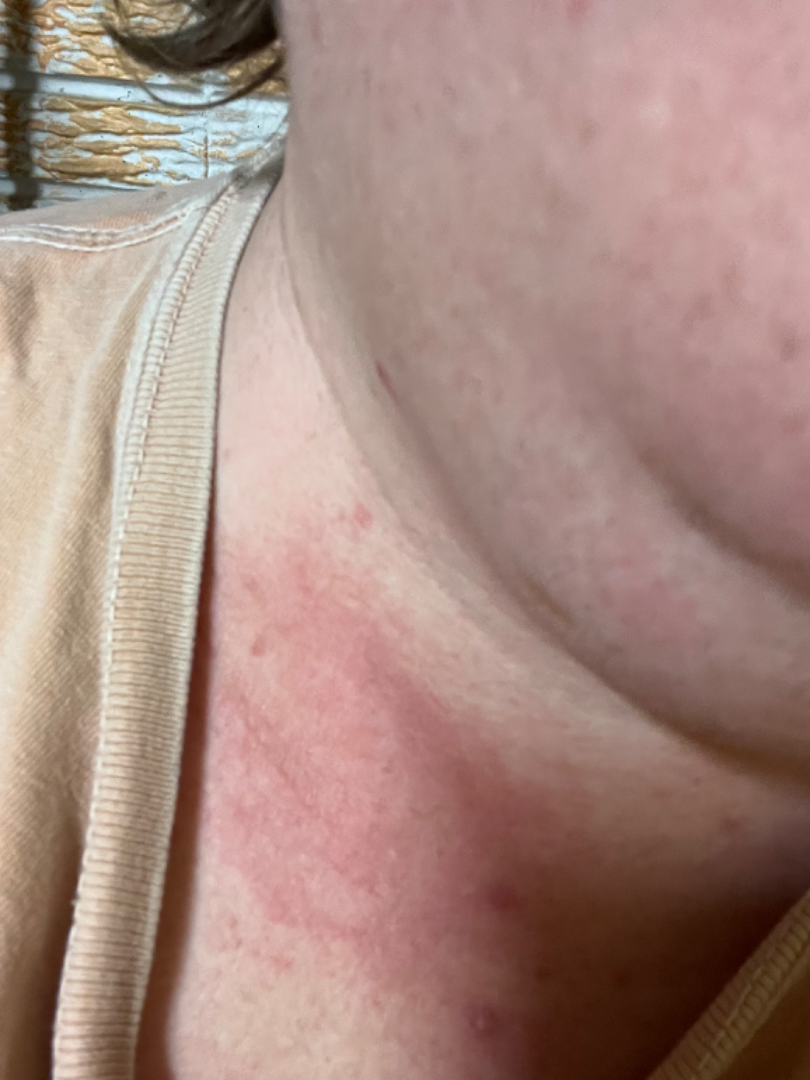Background:
The condition has been present for one to three months. The lesion involves the head or neck. Close-up view. The patient considered this a rash. Female contributor, age 30–39. Texture is reported as raised or bumpy. The lesion is associated with itching, burning and pain.
Findings:
On remote review of the image, Allergic Contact Dermatitis (possible); Irritant Contact Dermatitis (possible).